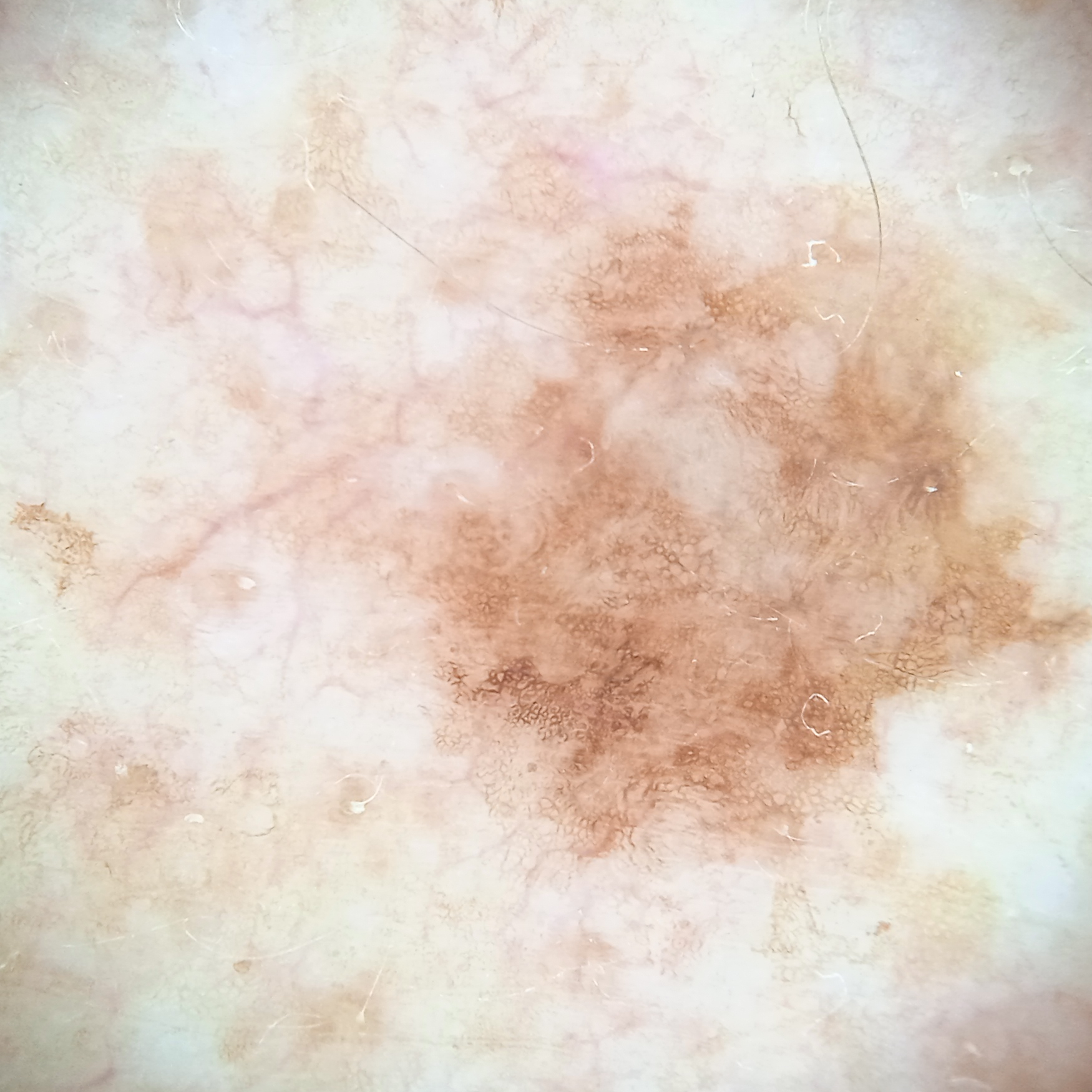The reviewing dermatologists could not reach a confident diagnosis. A male patient 81 years old. Few moles overall by the patient's own estimate. The patient says their skin reddens with sun exposure. By self-report, a family history of skin cancer, a personal history of cancer, no immunosuppression, and no personal history of skin cancer. Imaged for a research study, with no referral diagnosis recorded. A dermoscopic image of a skin lesion. The lesion is on the back. The lesion measures approximately 8 mm.